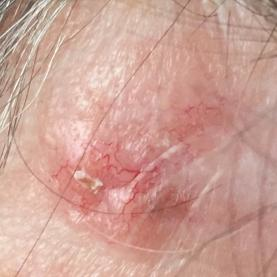A female subject 71 years of age. A clinical photograph showing a skin lesion. The lesion was found on the face. Per patient report, the lesion has grown, hurts, has bled, itches, and is elevated, but has not changed. On biopsy, the diagnosis was a basal cell carcinoma.